A smartphone photograph of a skin lesion. A subject in their late 70s.
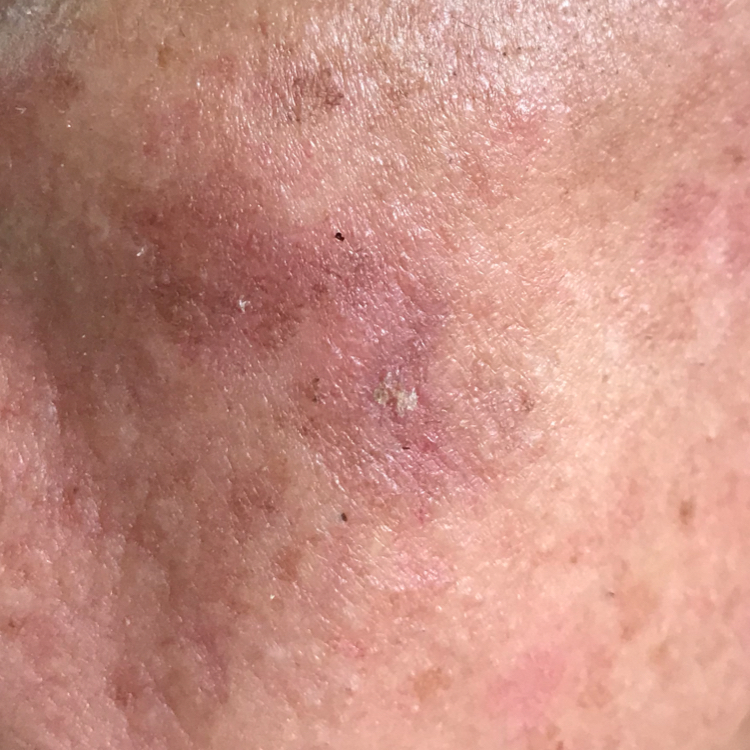site = the face, reported symptoms = itching, impression = actinic keratosis (clinical consensus).